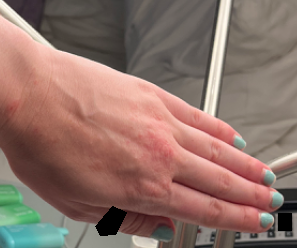{
  "body_site": "back of the hand",
  "shot_type": "at a distance",
  "patient": "female, age 30–39",
  "differential": {
    "leading": [
      "Allergic Contact Dermatitis"
    ],
    "considered": [
      "Eczema",
      "Irritant Contact Dermatitis"
    ]
  }
}